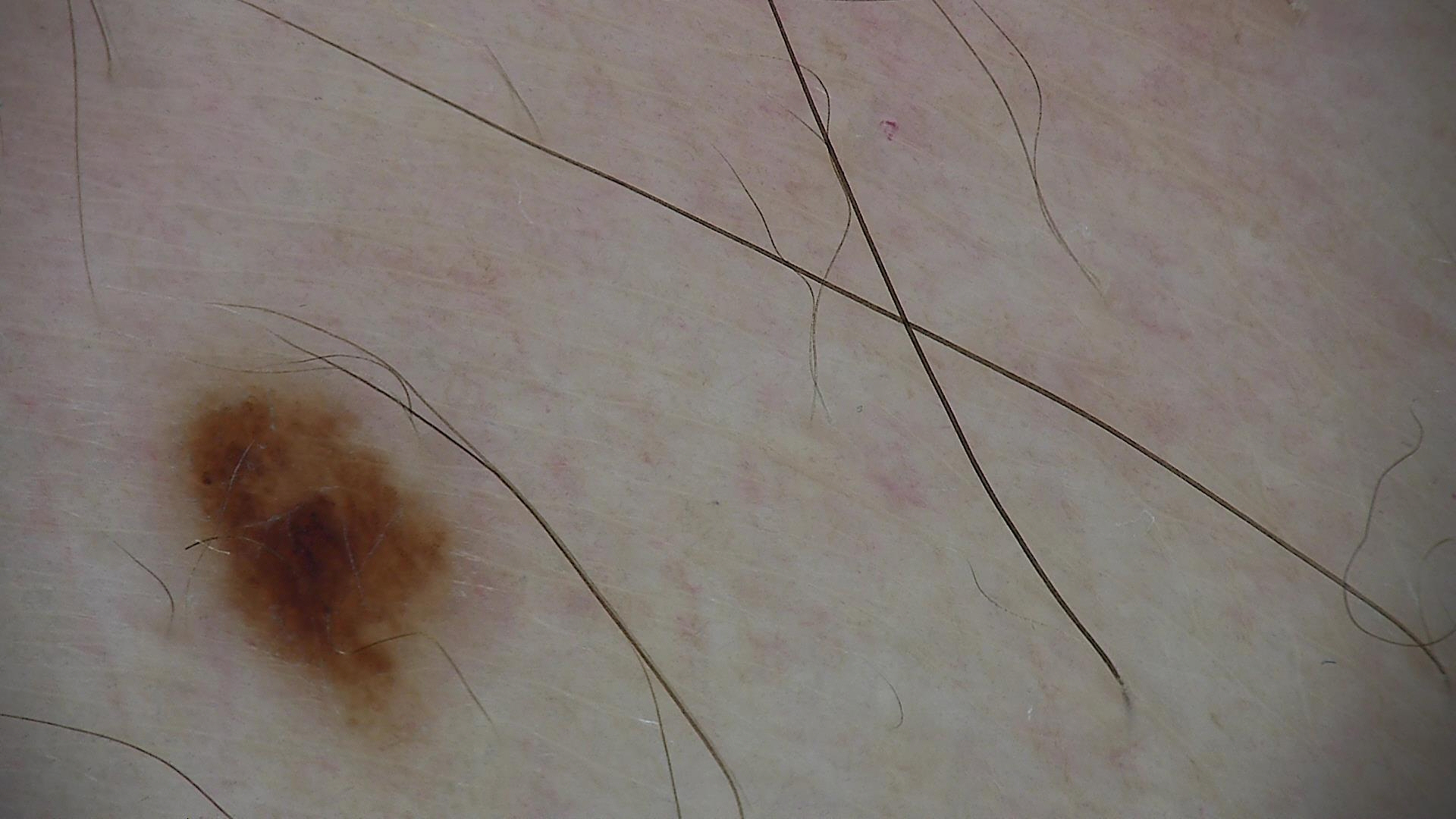Impression:
The diagnosis was a dysplastic junctional nevus.